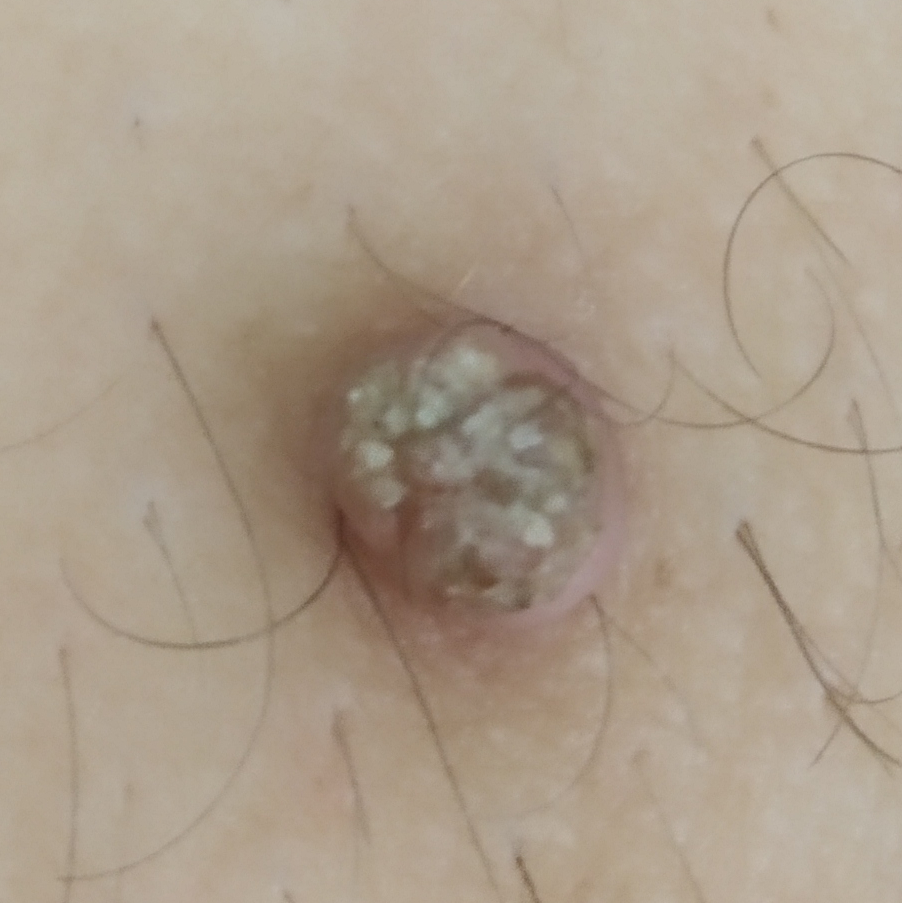{"patient": {"age": 59, "gender": "male"}, "skin_type": "III", "image": "smartphone clinical photo", "risk_factors": {"positive": ["alcohol use", "smoking"], "negative": ["pesticide exposure"]}, "lesion_location": "the abdomen", "lesion_size": {"diameter_1_mm": 5.0, "diameter_2_mm": 5.0}, "symptoms": {"present": ["bleeding", "growth", "elevation", "itching"], "absent": ["change in appearance", "pain"]}, "diagnosis": {"name": "actinic keratosis", "code": "ACK", "malignancy": "indeterminate", "confirmation": "histopathology"}}